The lesion involves the leg, arm and head or neck. The patient is a female aged 18–29. The photo was captured at an angle: 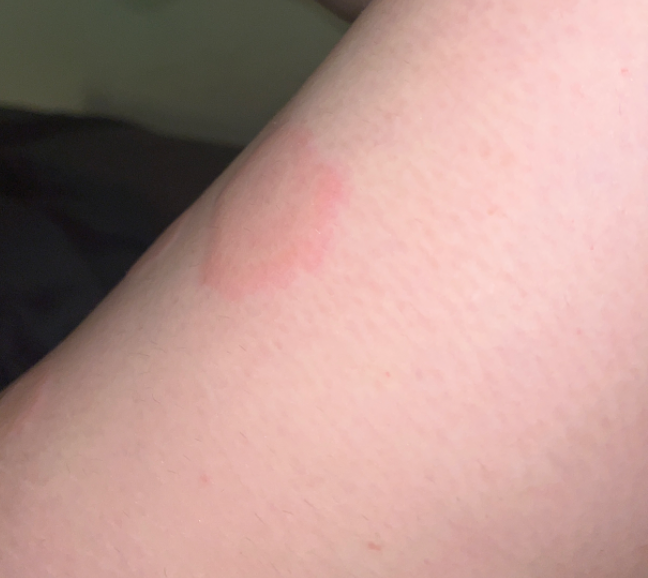Findings:
On remote review of the image, Drug Rash, Leukocytoclastic Vasculitis and Erythema multiforme were considered with similar weight.